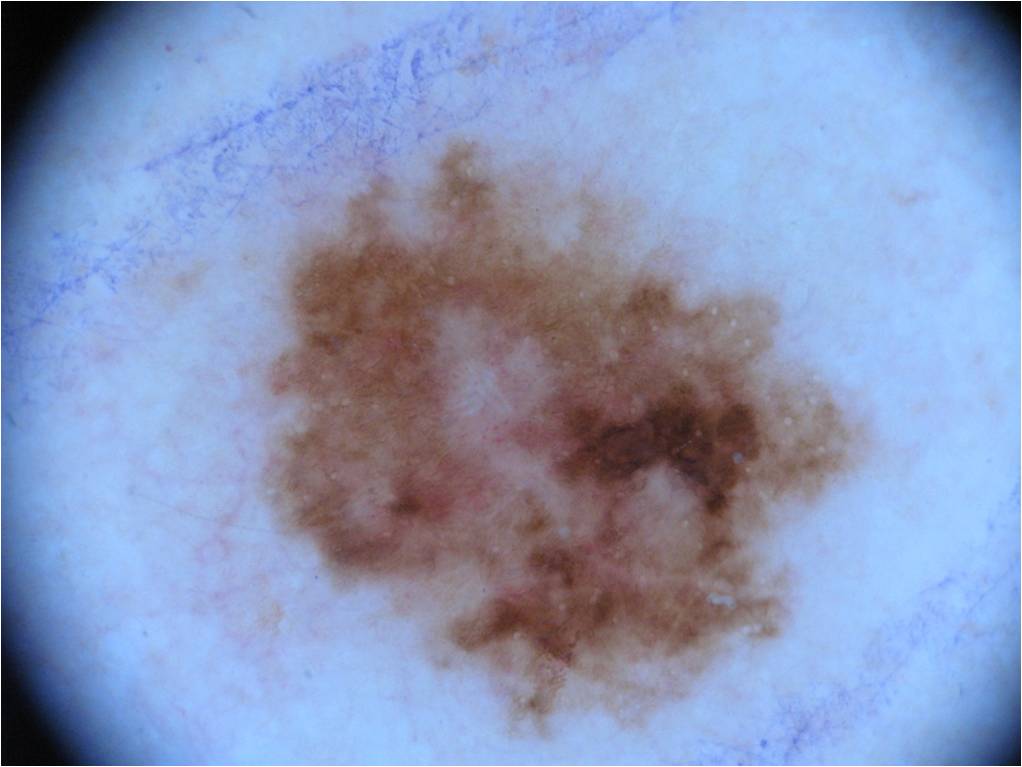Case summary:
– image · dermoscopic image
– location · [247, 136, 864, 733]
– diagnosis · a melanoma, a malignant skin lesion